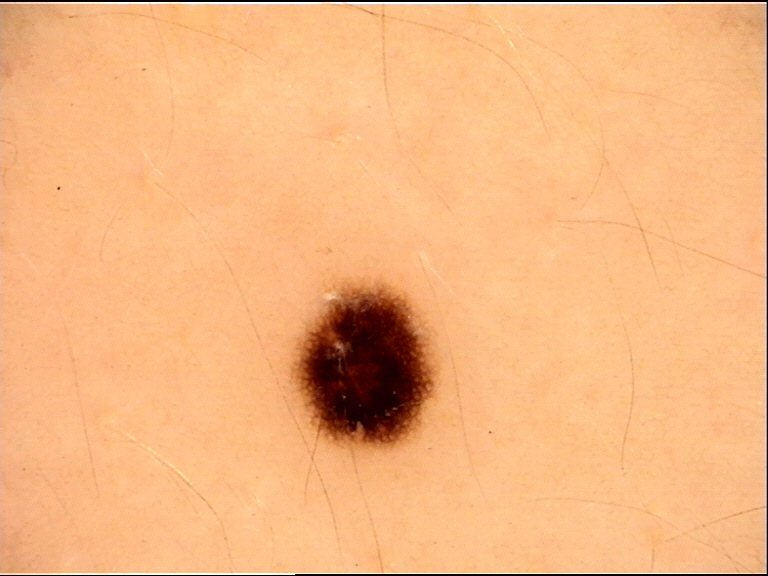Q: What kind of image is this?
A: dermatoscopy
Q: What kind of lesion is this?
A: banal
Q: What was the diagnostic impression?
A: junctional nevus (expert consensus)